Located on the back of the hand, arm, head or neck and leg · the photo was captured at an angle — 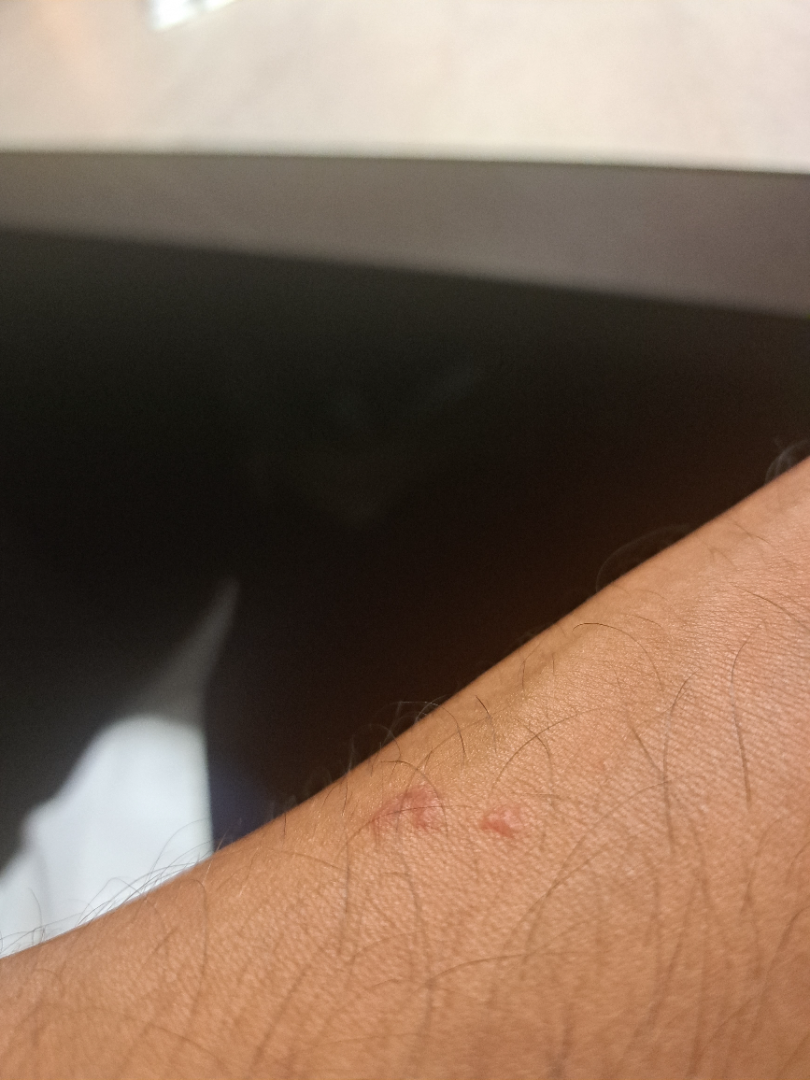Q: What was the assessment?
A: ungradable on photographic review
Q: Constitutional symptoms?
A: none reported
Q: Patient's own categorization?
A: a rash
Q: What is the lesion texture?
A: raised or bumpy and fluid-filled
Q: What symptoms does the patient report?
A: itching